The lesion involves the back of the hand and palm · an image taken at a distance · skin tone: Fitzpatrick skin type IV; lay reviewers estimated Monk Skin Tone 4–5 · reported duration is about one day · the patient is 18–29, female · the contributor notes the lesion is raised or bumpy:
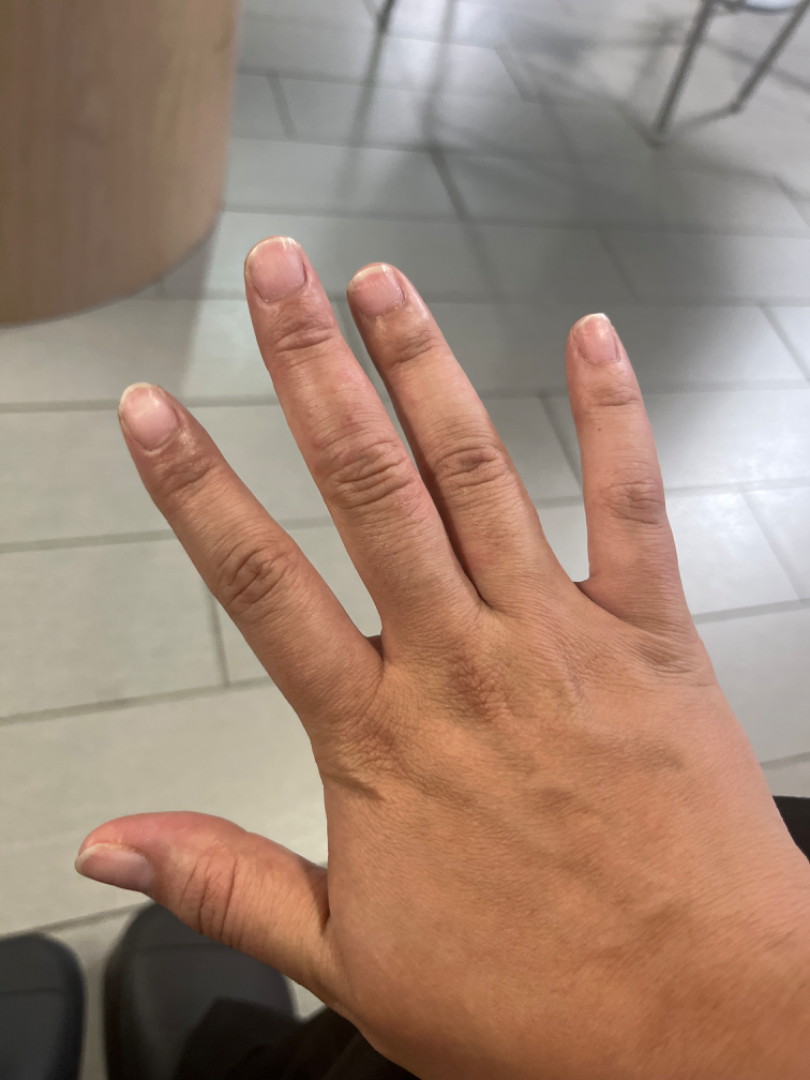On remote dermatologist review: Eczema (favored); Allergic Contact Dermatitis (possible).